The chart notes prior malignancy (patient or family) and no alcohol use · recorded as FST I · a smartphone photograph of a skin lesion · a female patient age 90.
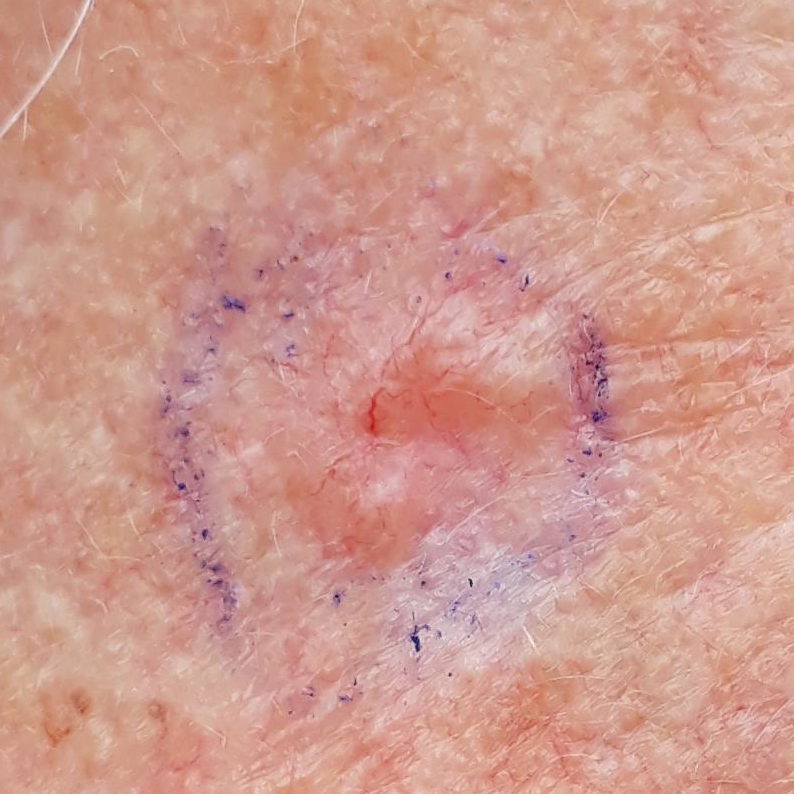site: the face
size: approx. 7 × 5 mm
patient-reported symptoms: itching, elevation
diagnostic label: basal cell carcinoma (biopsy-proven)